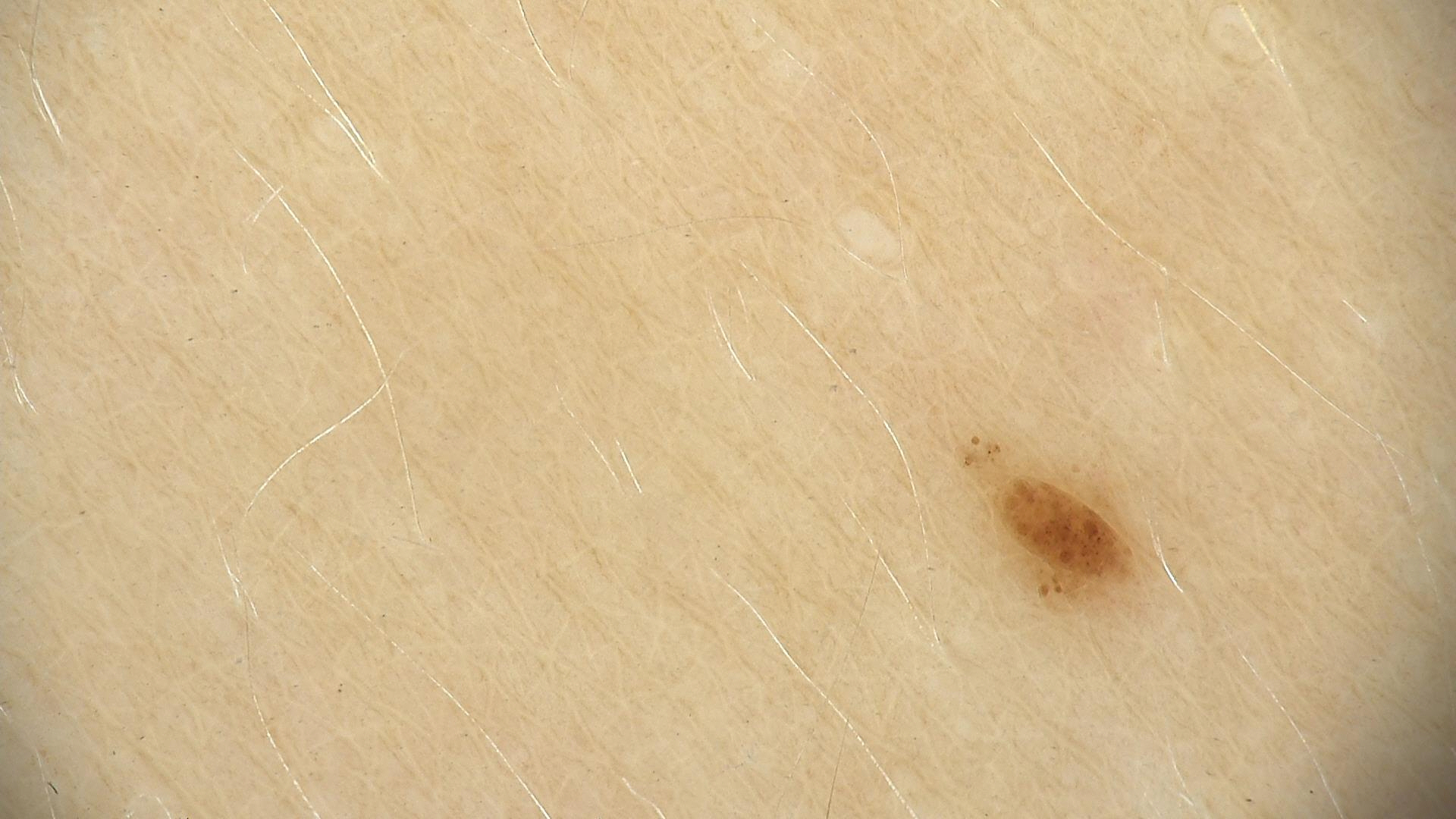A dermoscopy image of a single skin lesion. The diagnosis was a benign lesion — a dysplastic junctional nevus.